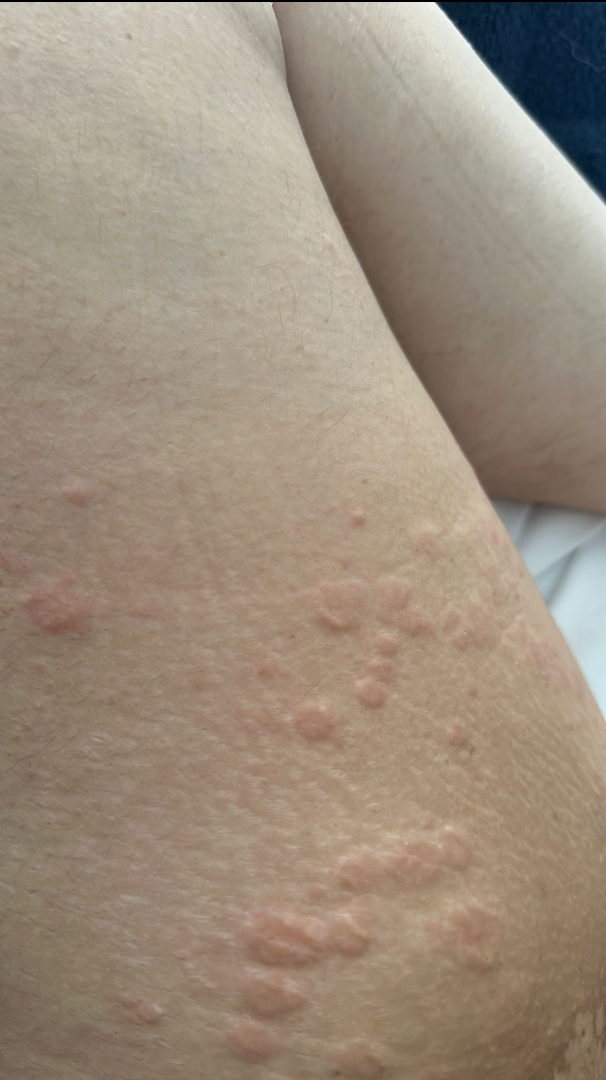- image framing — close-up
- assessment — Urticaria (1.00)